The lesion is associated with itching, human graders estimated MST 2–3, this is a close-up image, the lesion involves the leg and top or side of the foot, the patient considered this a rash, no relevant systemic symptoms, texture is reported as raised or bumpy.
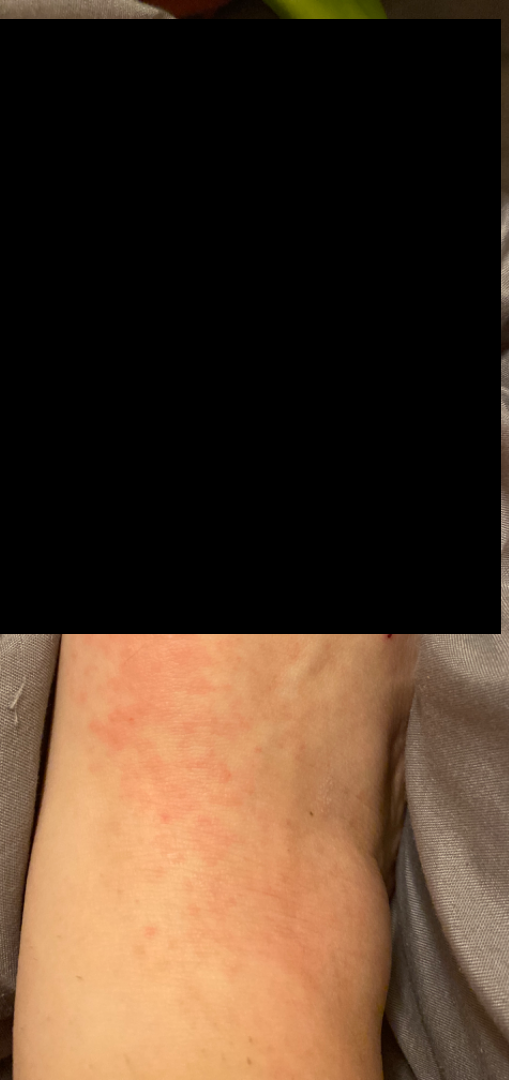assessment: could not be assessed.